An image taken at an angle; the top or side of the foot is involved:
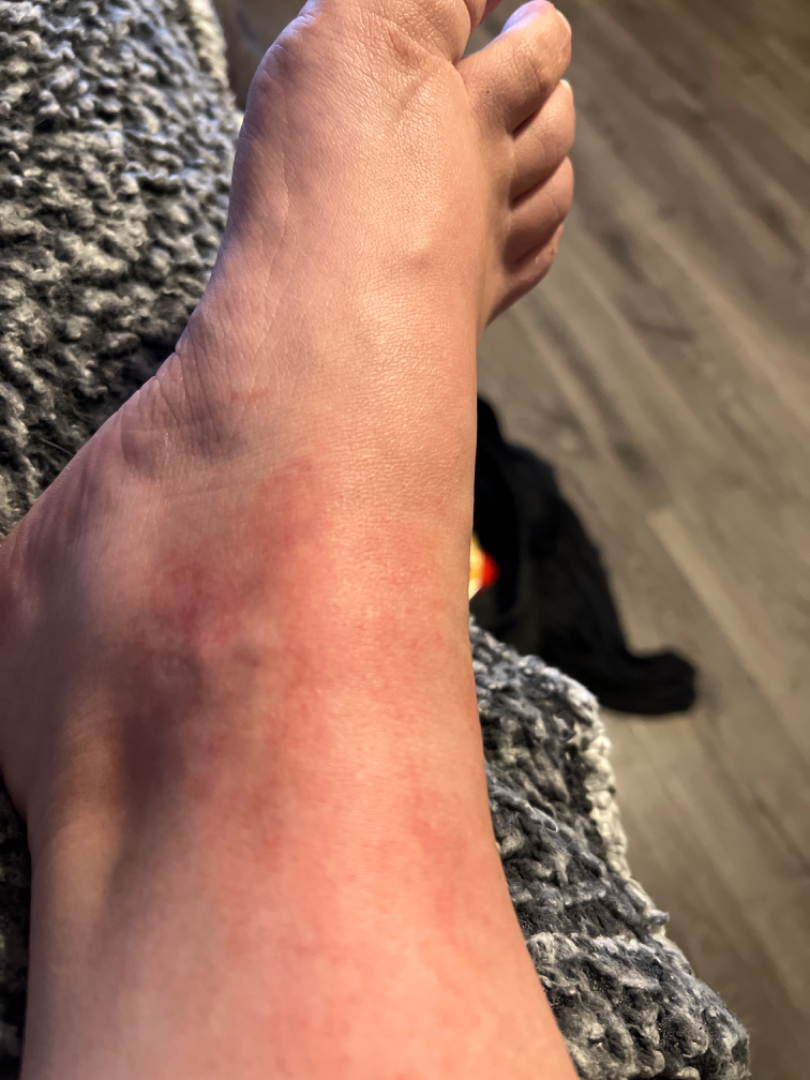Impression: The skin condition could not be confidently assessed from this image.